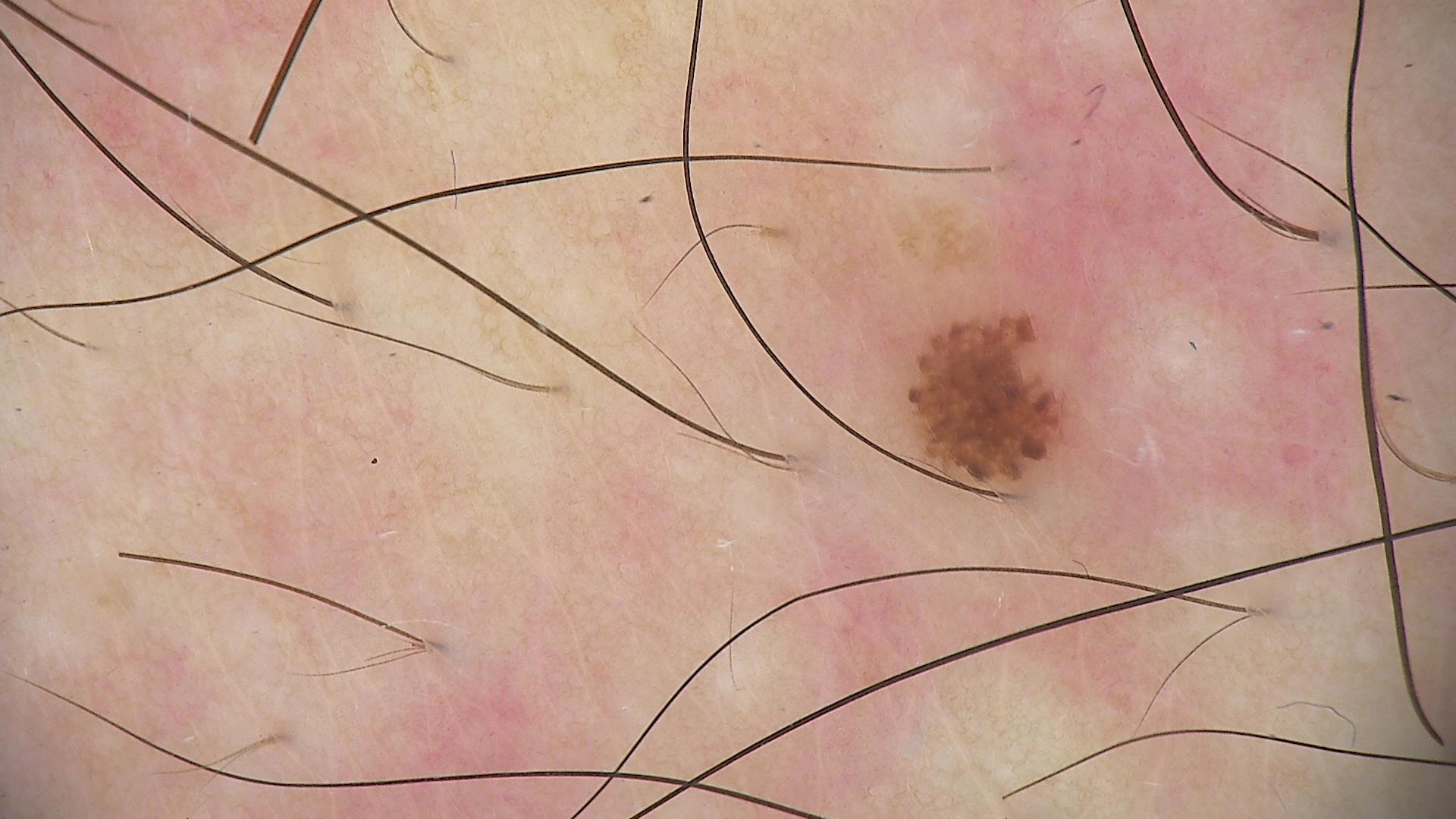The diagnostic label was a dysplastic junctional nevus.